A skin lesion imaged with a dermatoscope:
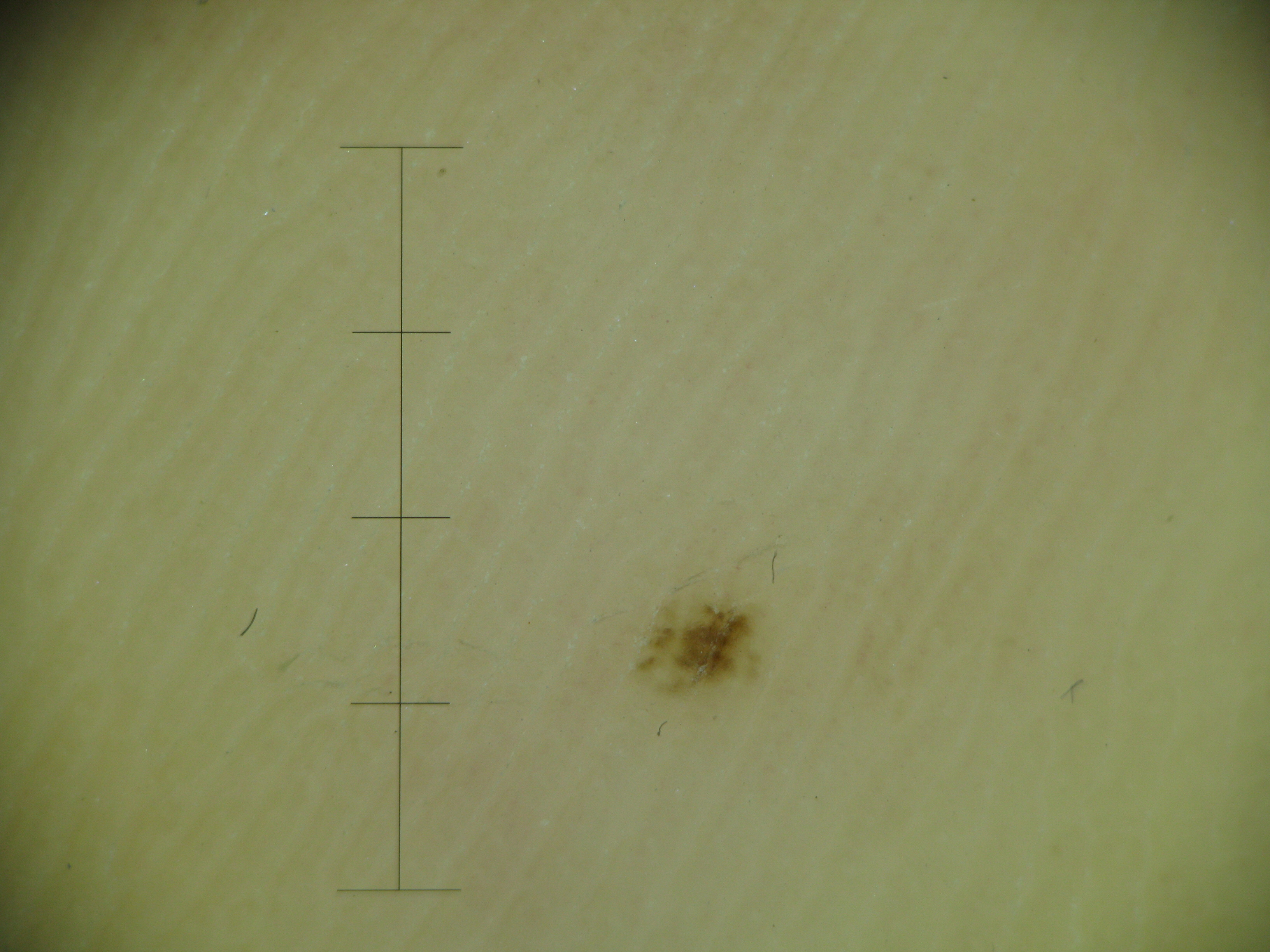The morphology is that of a banal lesion.
The diagnostic label was an acral junctional nevus.